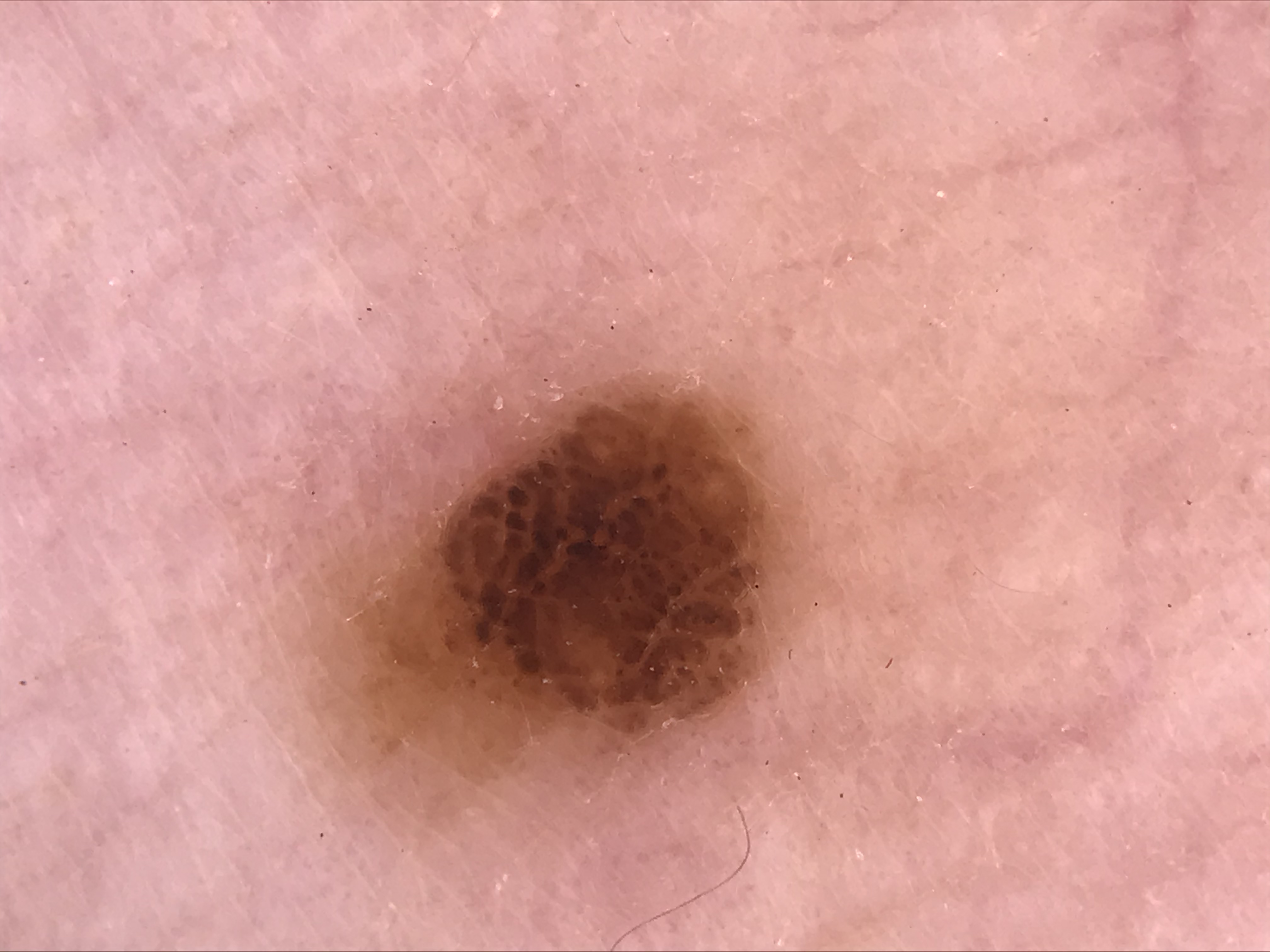diagnosis: compound nevus (expert consensus)